The photograph was taken at a distance; the contributor is 18–29, female; the affected area is the palm:
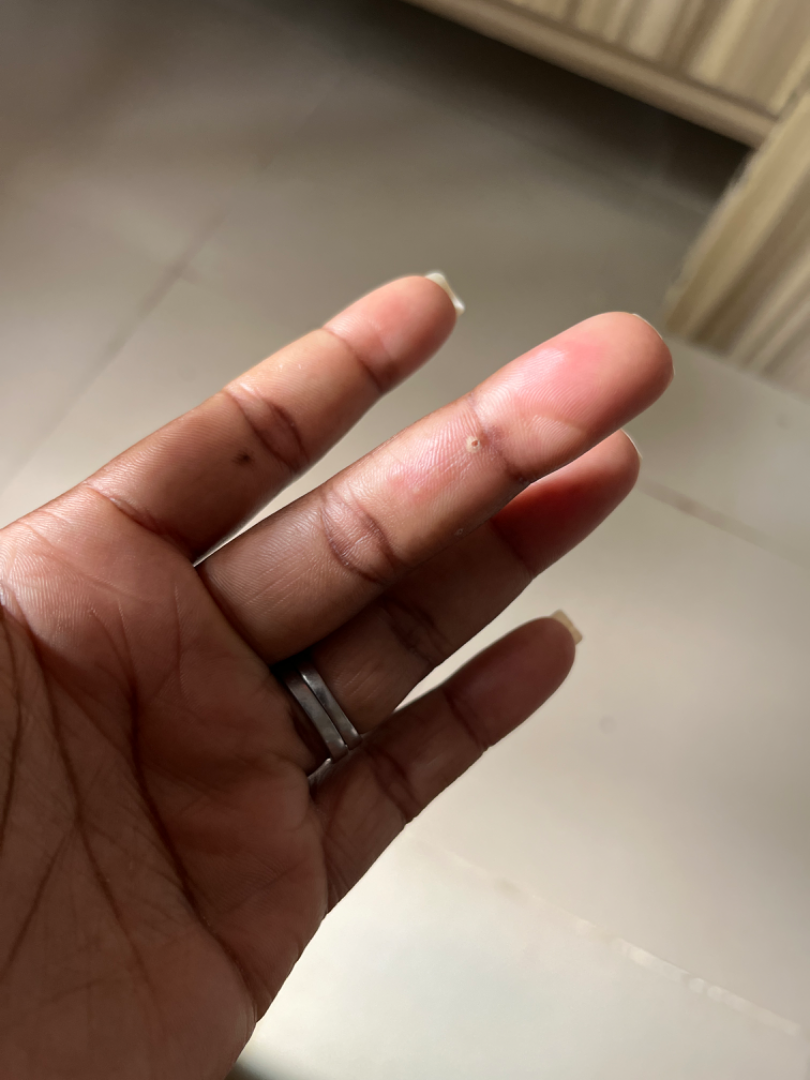Impression:
The differential, in no particular order, includes Impetigo and Foreign body.